A dermoscopy image of a single skin lesion:
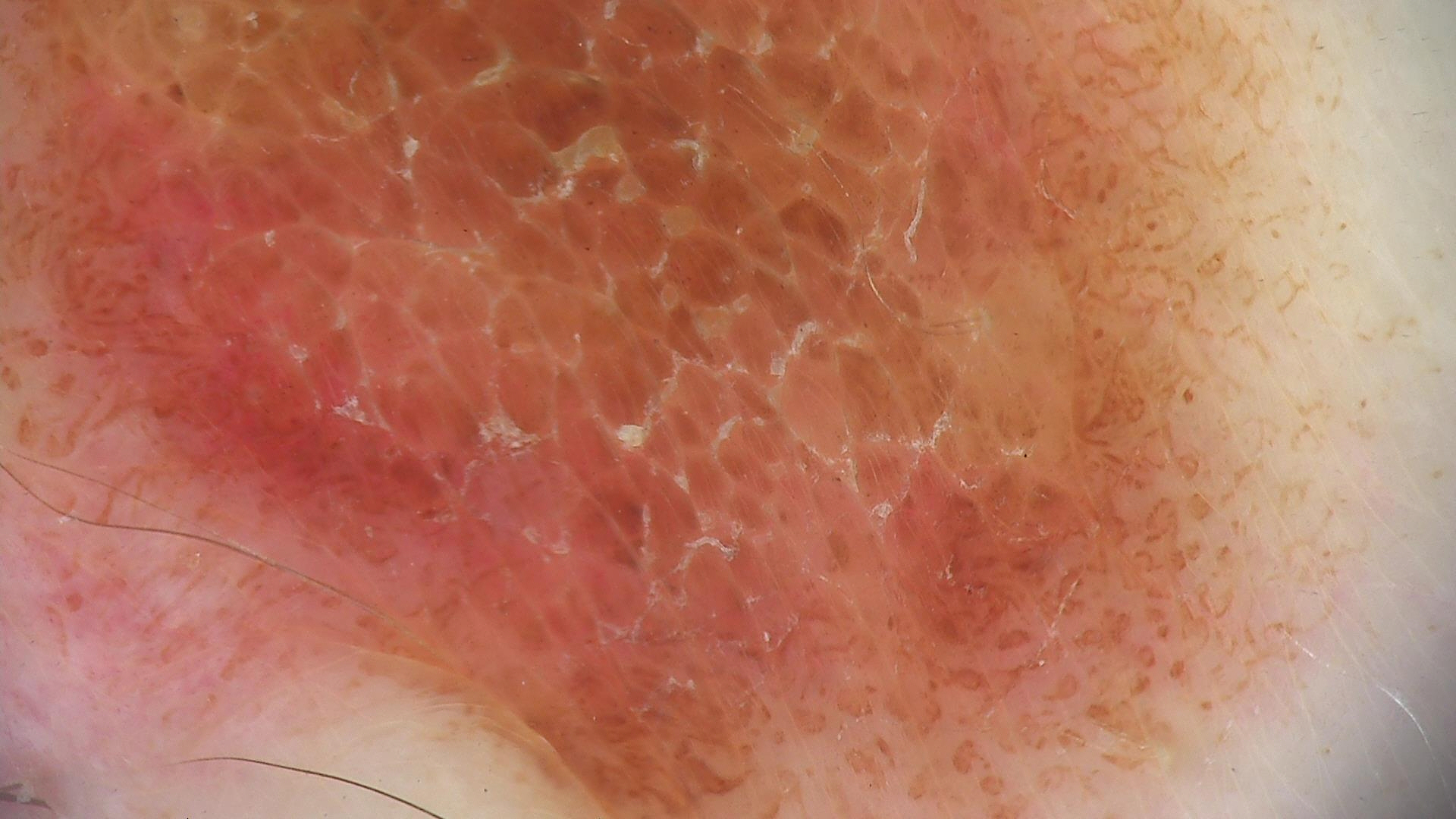Q: What is this lesion?
A: dysplastic compound nevus (expert consensus)